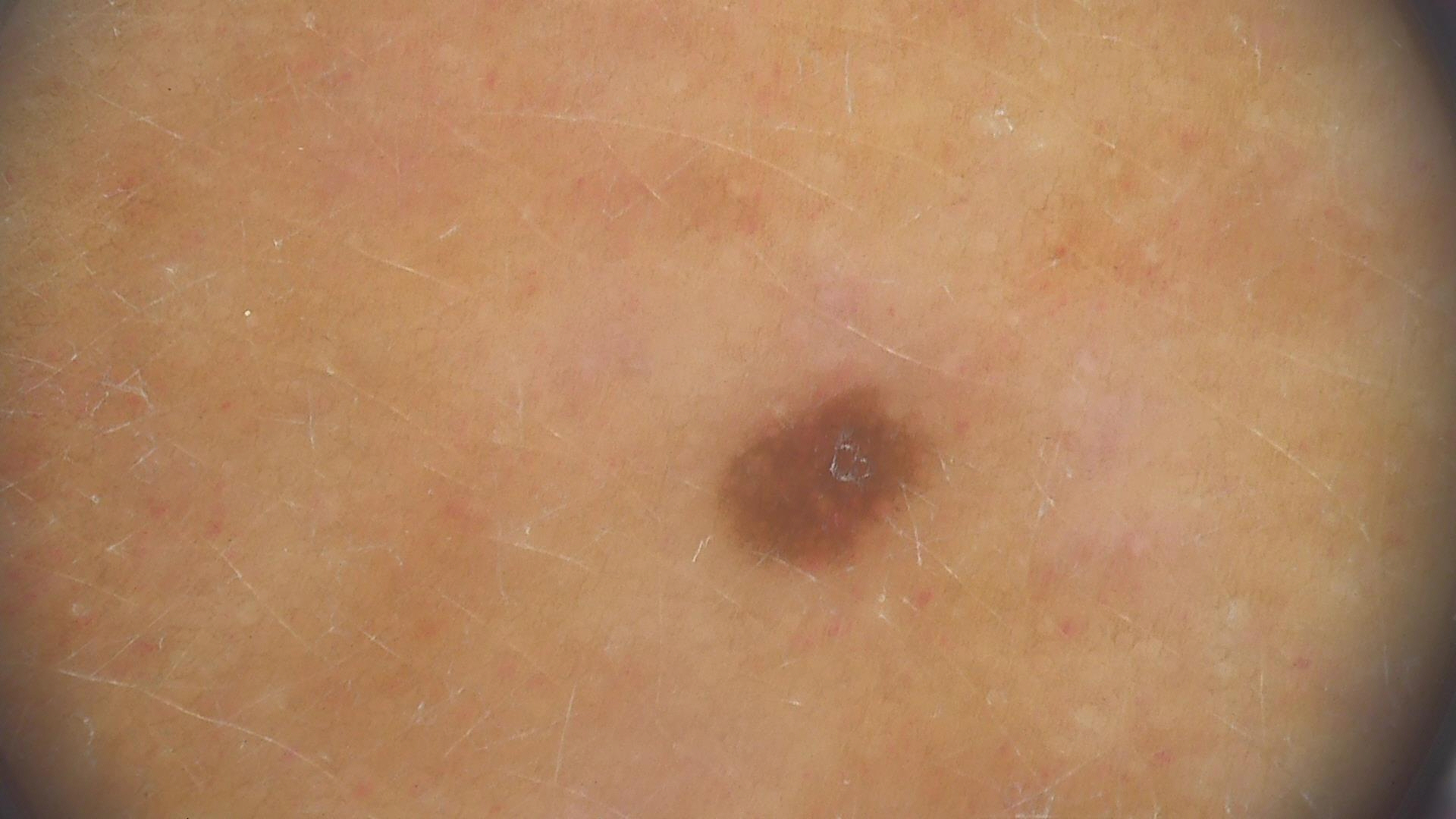Findings:
Dermoscopy of a skin lesion.
Conclusion:
Classified as a banal lesion — a junctional nevus.